This is a close-up image: 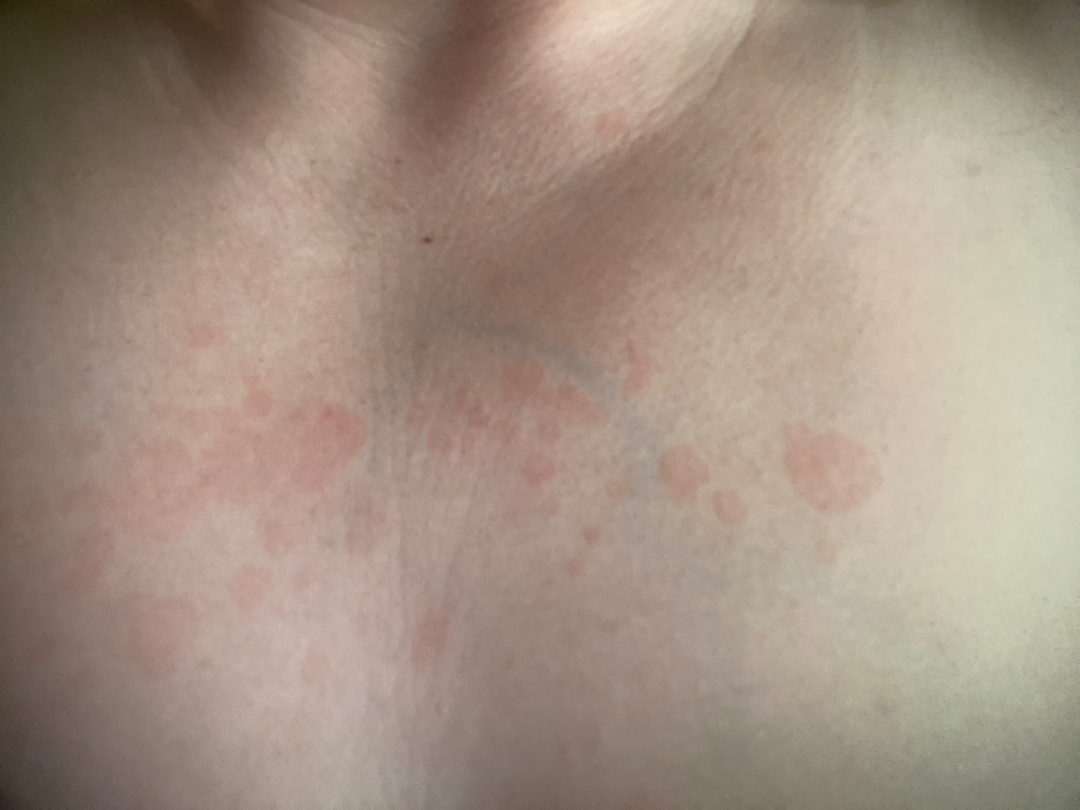Notes:
– assessment · Tinea Versicolor (1.00)